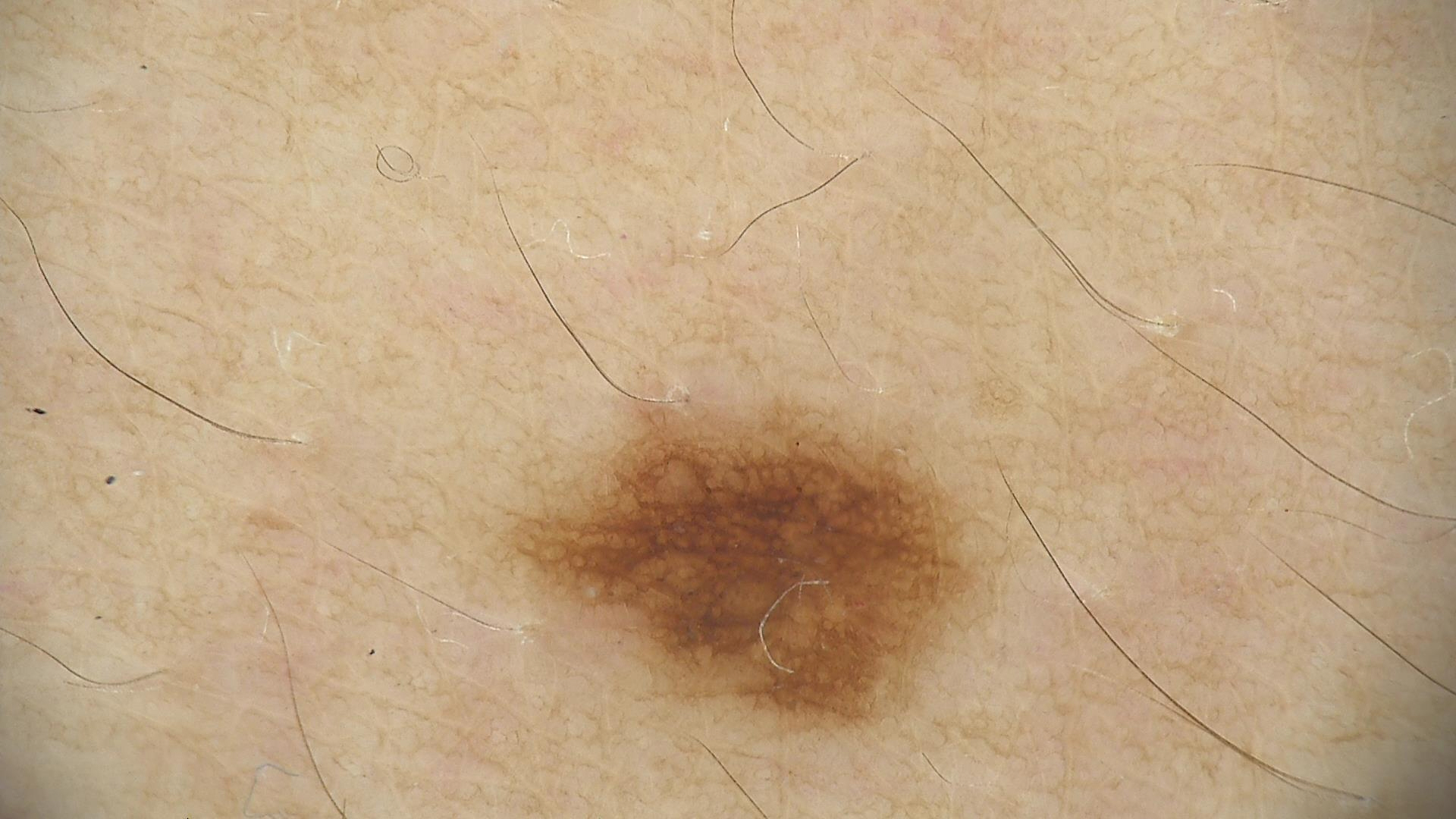Q: What kind of image is this?
A: dermatoscopy
Q: What is this lesion?
A: dysplastic junctional nevus (expert consensus)